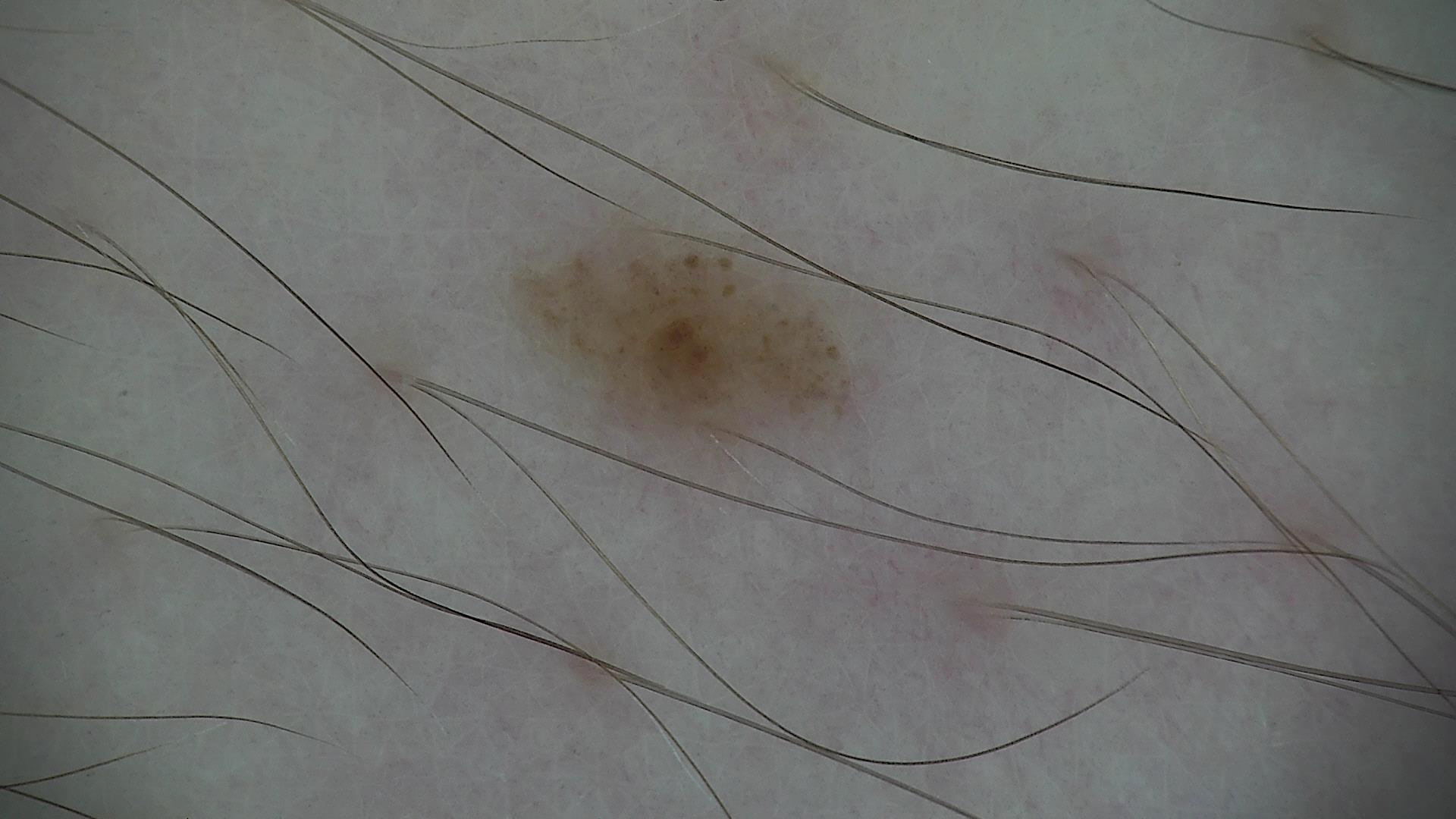A dermatoscopic image of a skin lesion. Classified as a dysplastic junctional nevus.